The photograph is a close-up of the affected area, the front of the torso and back of the torso are involved:
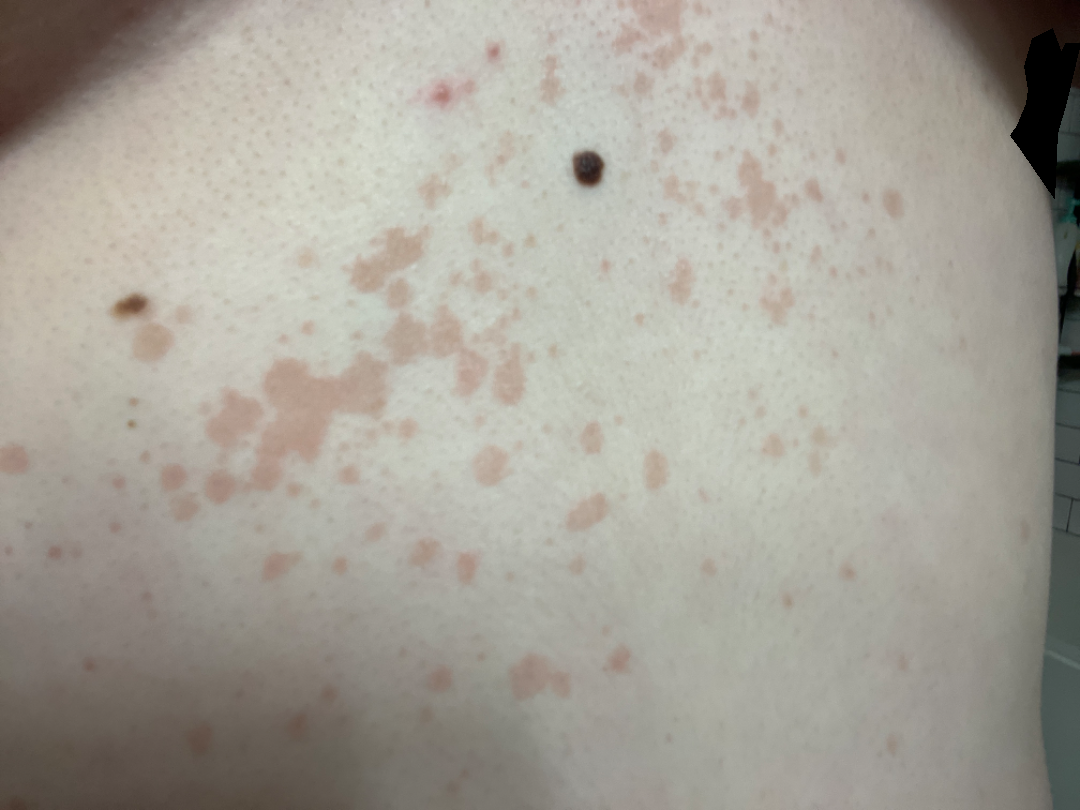patient-reported symptoms = darkening, itching and enlargement
lesion texture = raised or bumpy and rough or flaky
patient describes the issue as = a rash
diagnostic considerations = three dermatologists independently reviewed the case: the leading impression is Tinea Versicolor; less likely is Drug Rash; less probable is Seborrheic Dermatitis; lower on the differential is Psoriasis